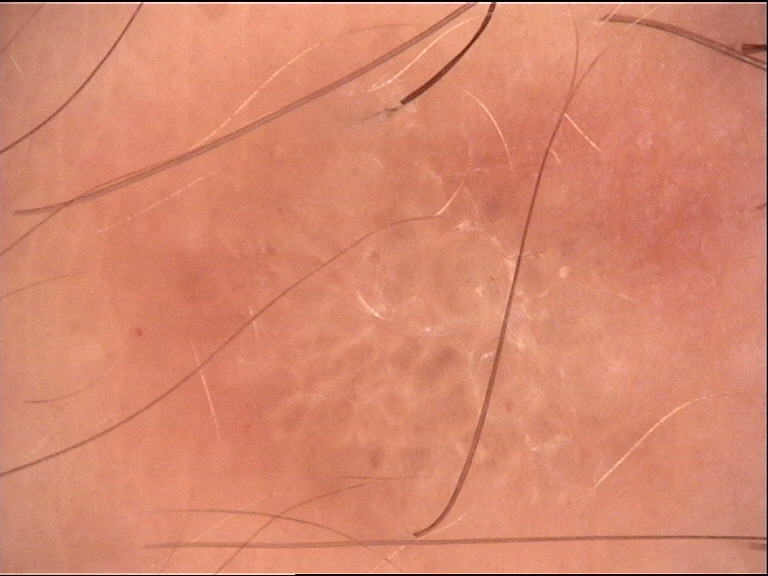<dermoscopy>
<image>dermatoscopy</image>
<diagnosis>
<name>dermatofibroma</name>
<code>df</code>
<malignancy>benign</malignancy>
<super_class>non-melanocytic</super_class>
<confirmation>expert consensus</confirmation>
</diagnosis>
</dermoscopy>